The patient is Fitzpatrick skin type II. Dermoscopy of a skin lesion. A female subject aged 83 or older — 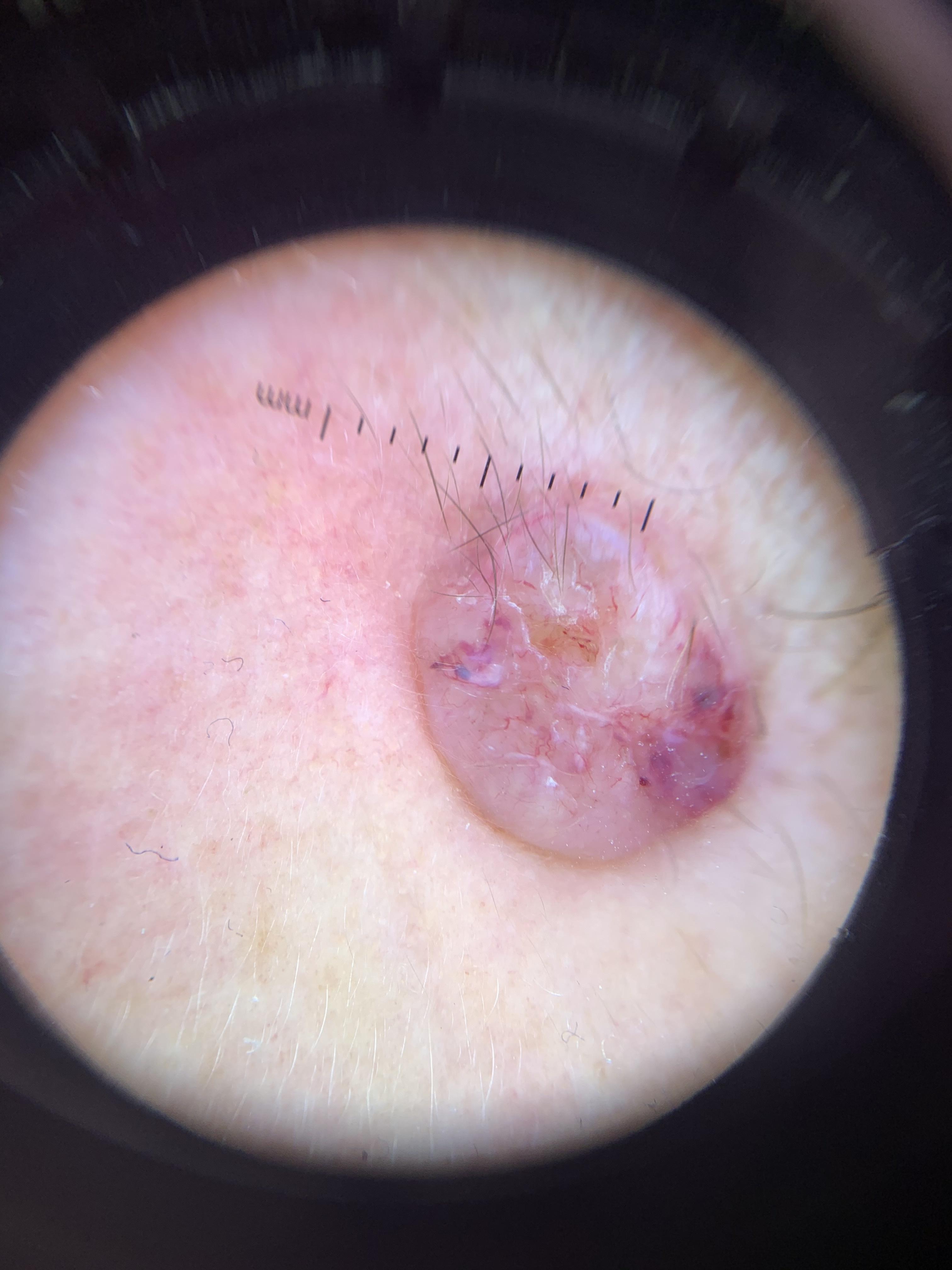Findings:
– body site — the head or neck
– pathology — Basal cell carcinoma (biopsy-proven)